A female patient aged around 75. The patient was assessed as Fitzpatrick phototype II — 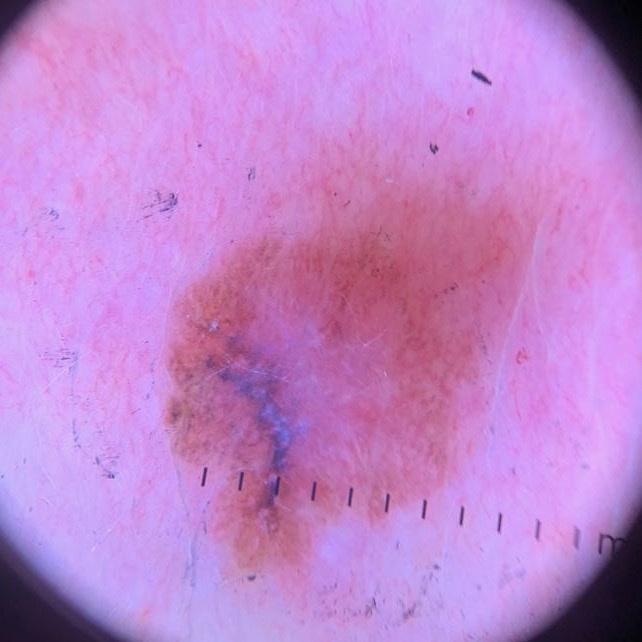lesion_location:
  region: the trunk
  detail: the posterior trunk
diagnosis:
  name: Melanoma
  malignancy: malignant
  confirmation: histopathology